Dermoscopy of a skin lesion. A male patient aged 43-47 — 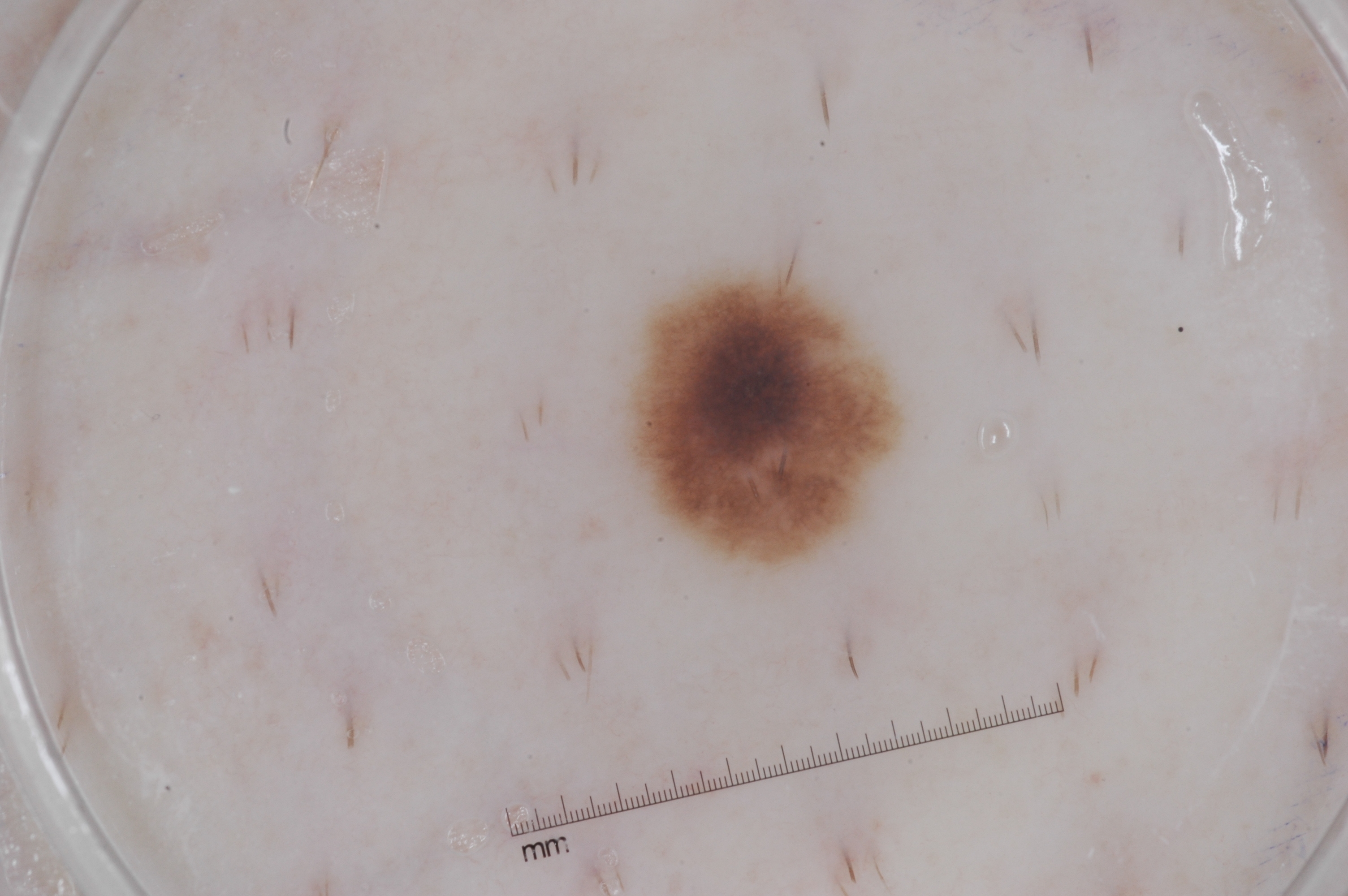- features — pigment network
- size — ~5% of the field
- lesion location — box(633, 266, 895, 567)
- diagnosis — a melanocytic nevus